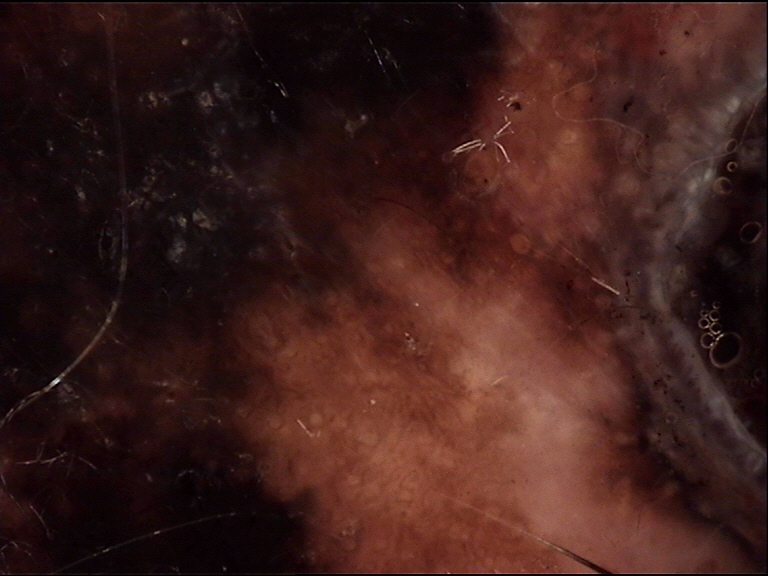Confirmed on histopathology as a lentigo maligna melanoma.